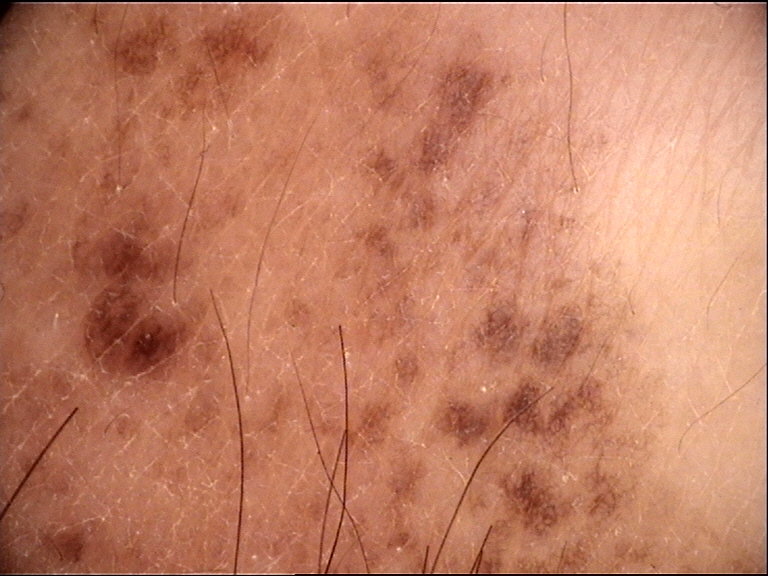- modality · dermoscopy
- lesion type · banal
- label · congenital compound nevus (expert consensus)